A male patient 15 years of age; a clinical close-up of a skin lesion; the referring clinician suspected melanocytic nevus: 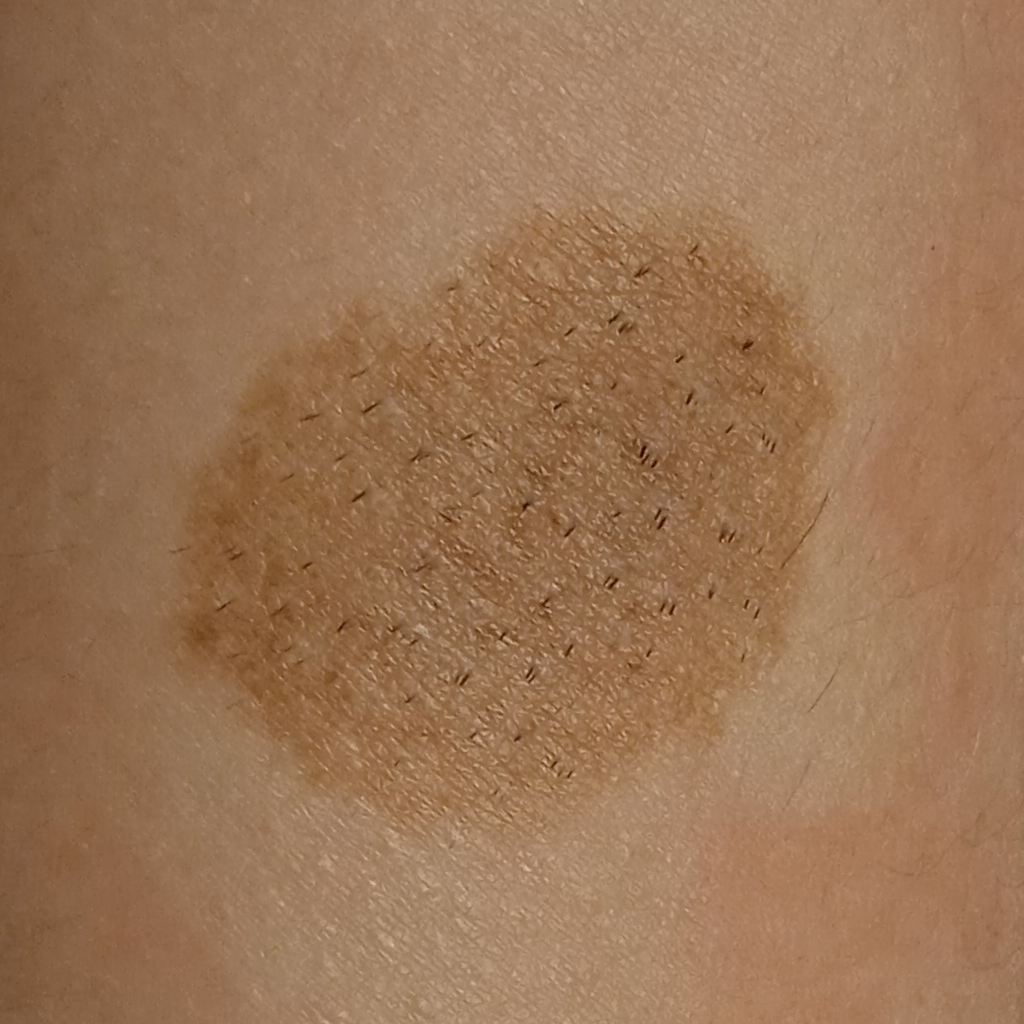- diameter — 26.1 mm
- pathology — melanocytic nevus (biopsy-proven)